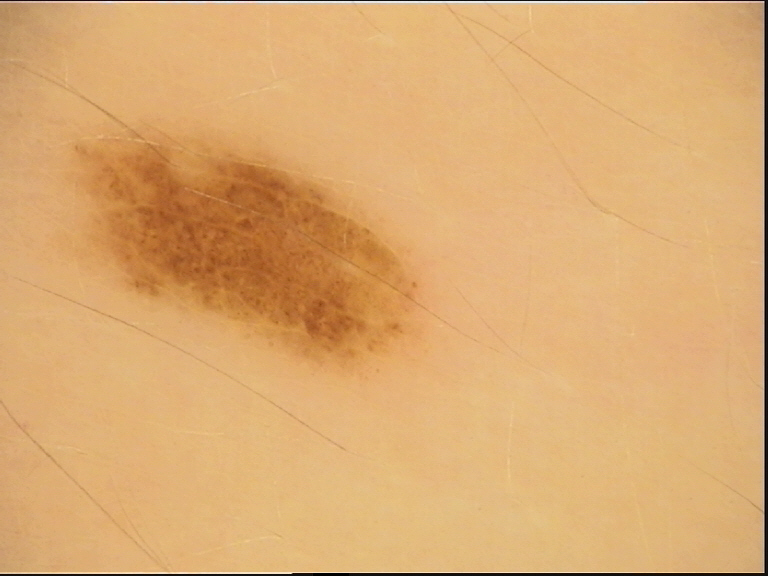| field | value |
|---|---|
| imaging | dermatoscopy |
| category | banal |
| diagnosis | junctional nevus (expert consensus) |